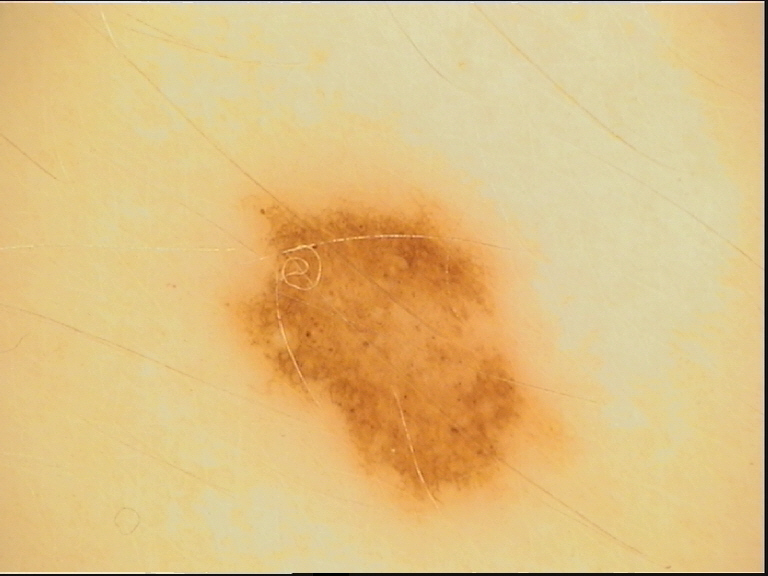A dermoscopic image of a skin lesion.
Consistent with a dysplastic junctional nevus.